The photograph is a close-up of the affected area; the patient is female; the patient described the issue as a rash; the contributor notes the condition has been present for less than one week; the lesion is described as rough or flaky — 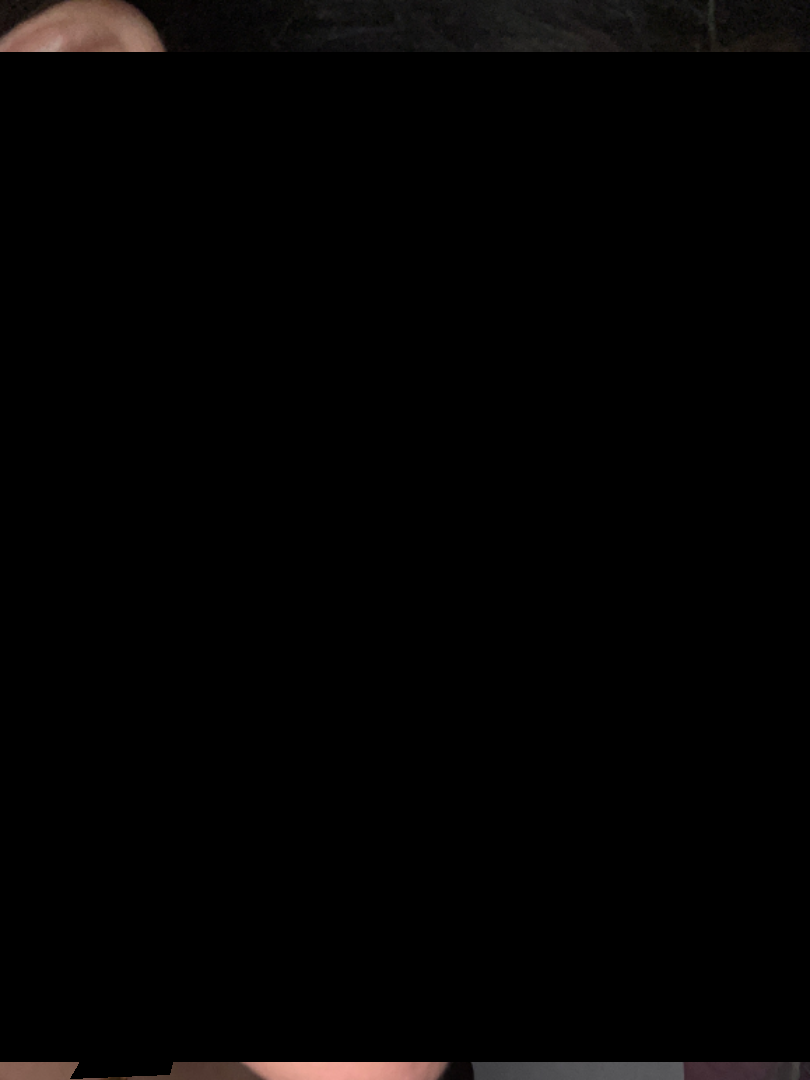No skin condition was discernible on photographic review.